The subject is a male aged around 15 · a dermoscopy image of a single skin lesion: 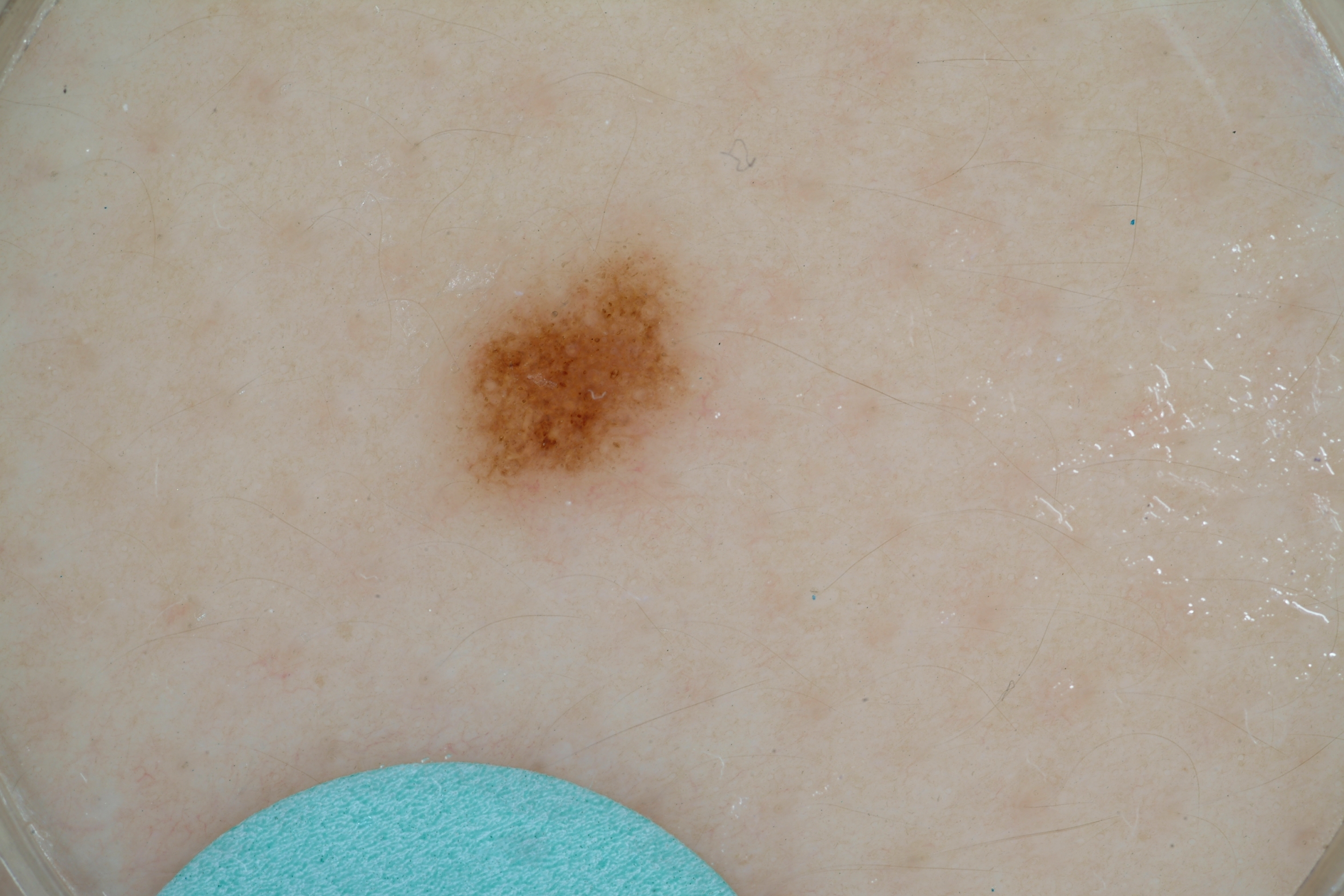| field | value |
|---|---|
| absent dermoscopic features | milia-like cysts, pigment network, streaks, and negative network |
| lesion extent | ~6% of the field |
| location | [427,219,720,522] |
| impression | a melanocytic nevus |